Reported duration is more than one year. The patient also reports fatigue, shortness of breath, fever, joint pain and mouth sores. The head or neck is involved. Texture is reported as fluid-filled, raised or bumpy and rough or flaky. The photograph is a close-up of the affected area. Female subject, age 40–49. Reported lesion symptoms include enlargement, bothersome appearance and pain:
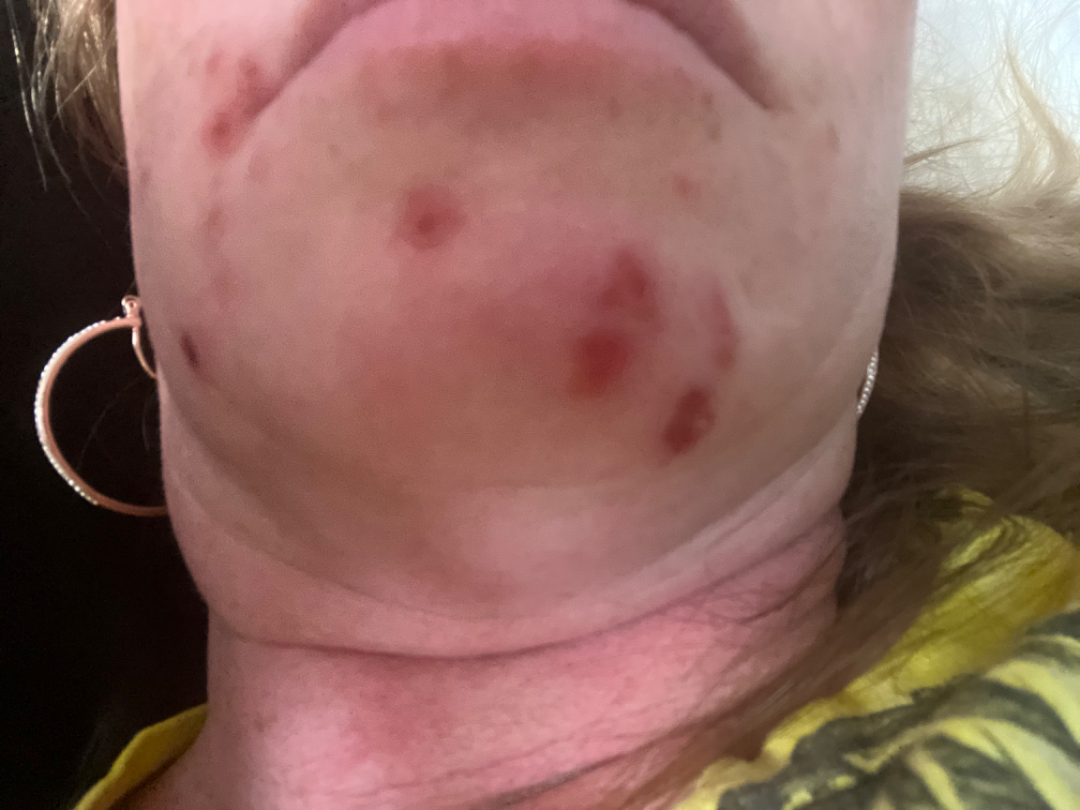Most consistent with Acne.